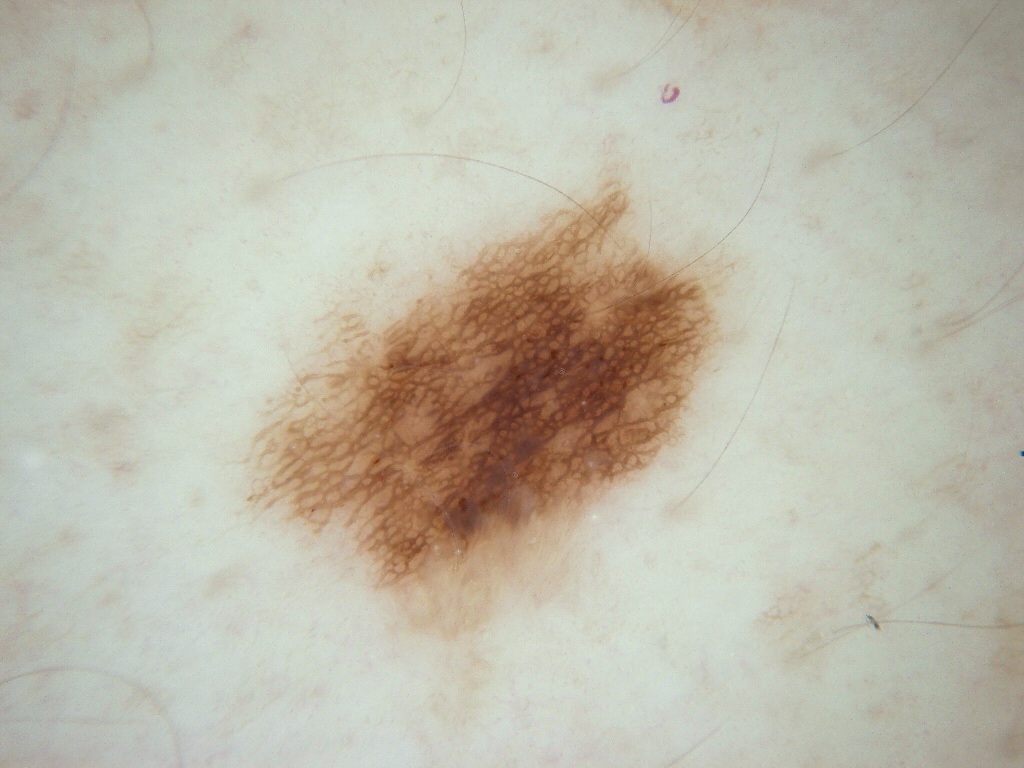A dermoscopic image of a skin lesion.
A female patient, aged 63-67.
In (x1, y1, x2, y2) order, the lesion occupies the region 248, 175, 725, 637.
Dermoscopically, the lesion shows milia-like cysts and pigment network.
Consistent with a melanocytic nevus, a benign skin lesion.